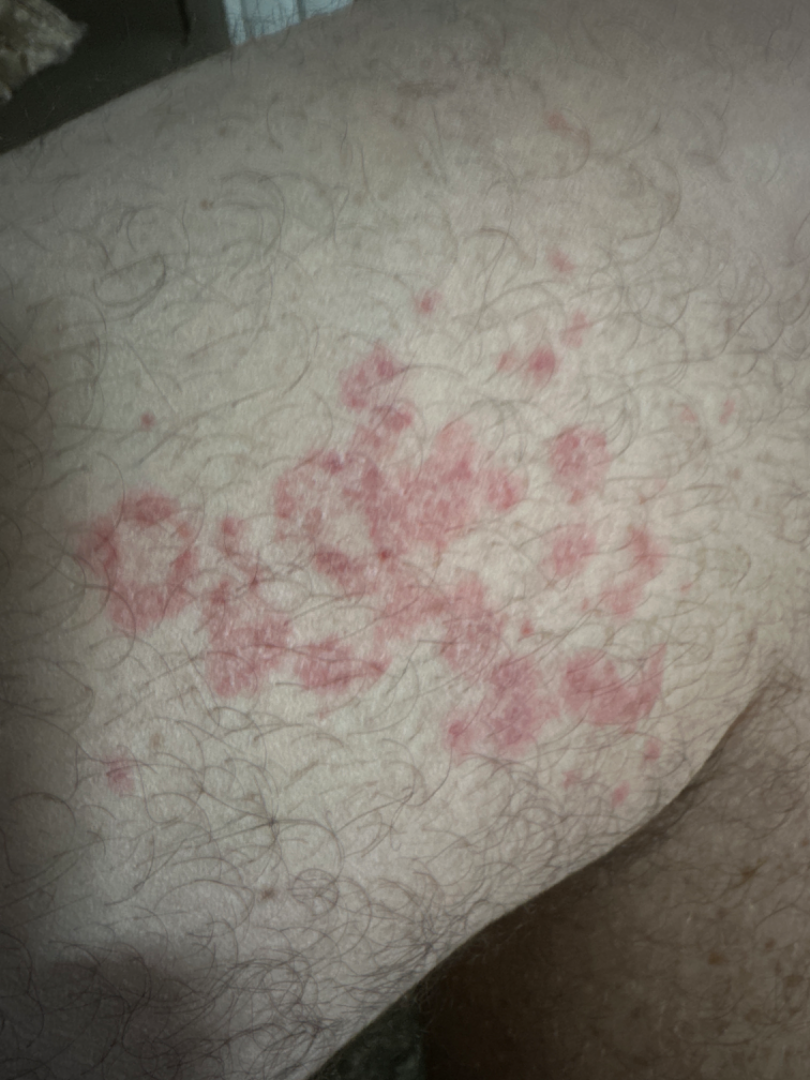<summary>
<texture>flat</texture>
<duration>less than one week</duration>
<body_site>leg</body_site>
<systemic_symptoms>none reported</systemic_symptoms>
<patient>male, age 40–49</patient>
<shot_type>close-up</shot_type>
<differential>
  <leading>Granuloma annulare</leading>
  <considered>Annular erythema</considered>
</differential>
</summary>